The lesion involves the front of the torso, leg, back of the torso, arm, head or neck, palm and back of the hand; this image was taken at a distance; the contributor is male: 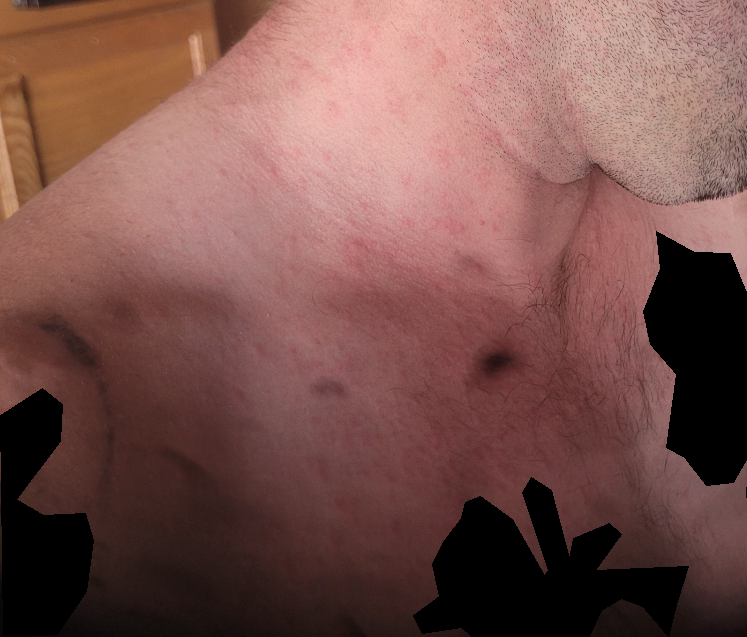Contact dermatitis (primary).